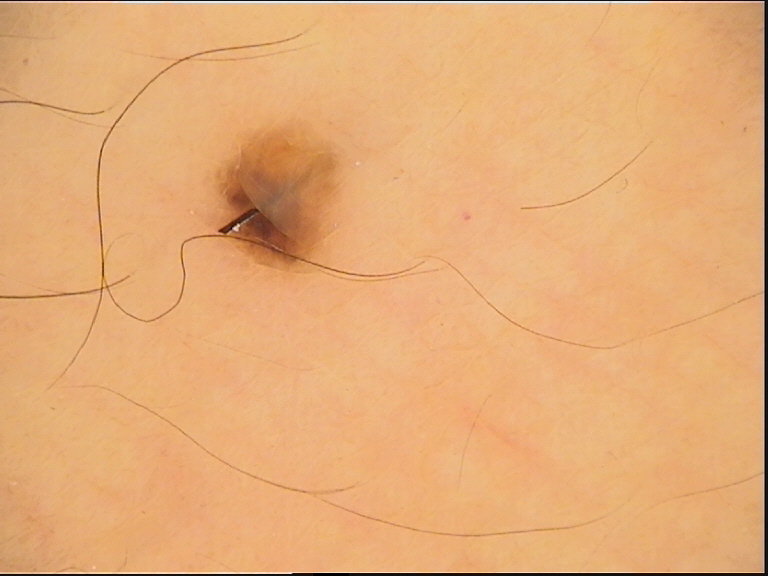subtype = banal | label = compound nevus (expert consensus).